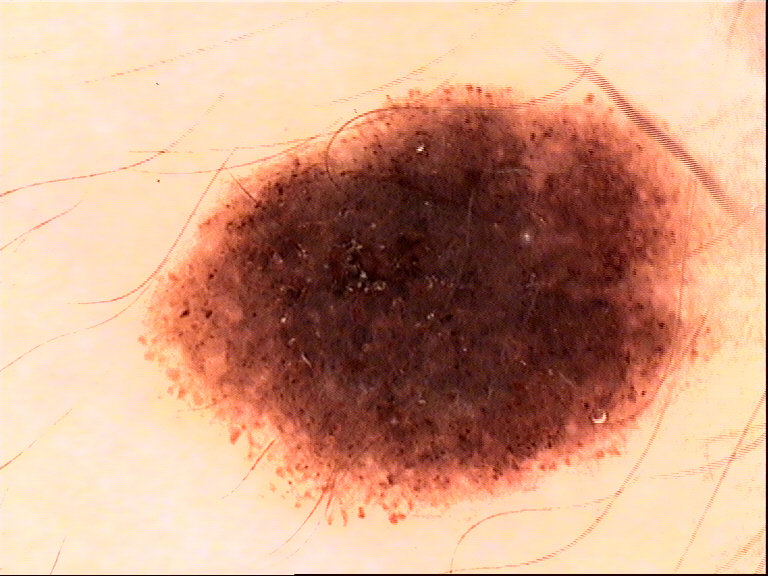A dermatoscopic image of a skin lesion. The diagnostic label was a benign lesion — a dysplastic compound nevus.